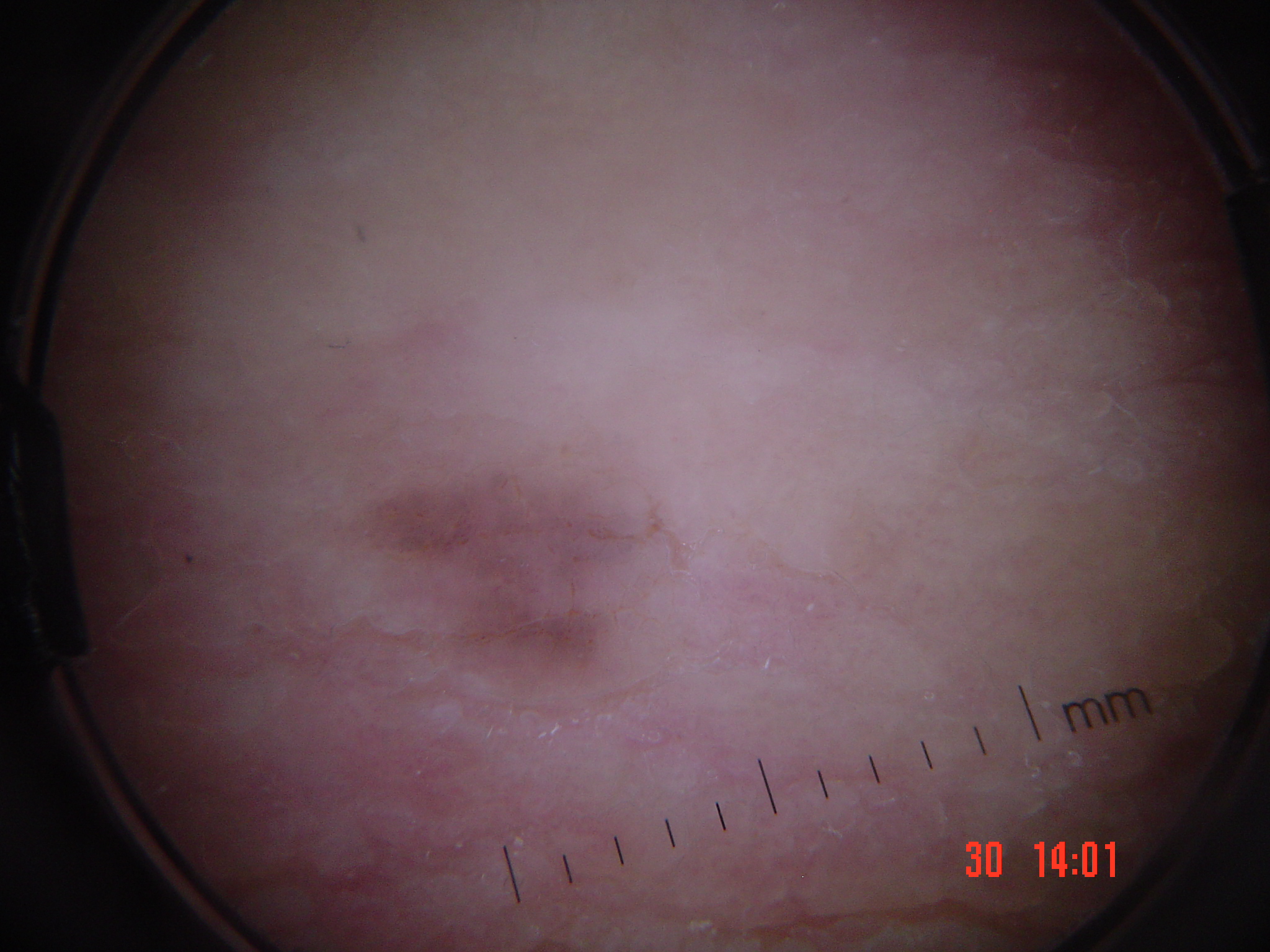A skin lesion imaged with a dermatoscope. The diagnosis was a seborrheic keratosis.